A female patient aged approximately 25 · a skin lesion imaged with a dermatoscope.
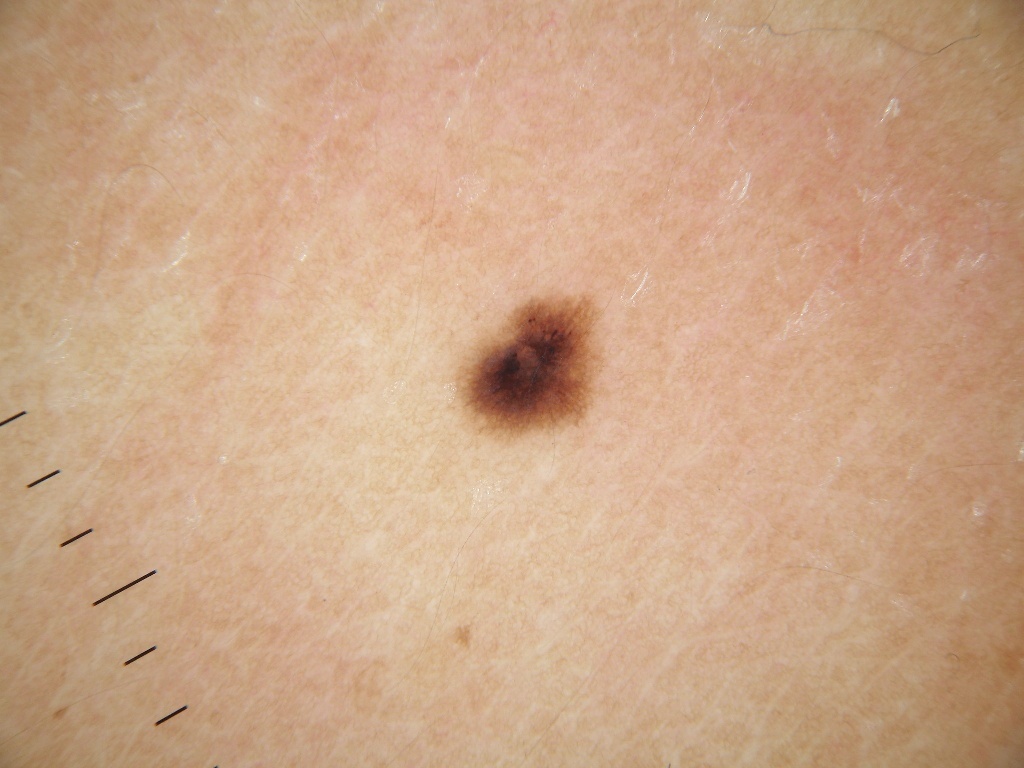A small lesion within a wider field of skin.
On dermoscopy, the lesion shows pigment network, with no globules, negative network, milia-like cysts, or streaks.
The lesion's extent is x1=456, y1=295, x2=597, y2=437.
Clinically diagnosed as a melanocytic nevus.